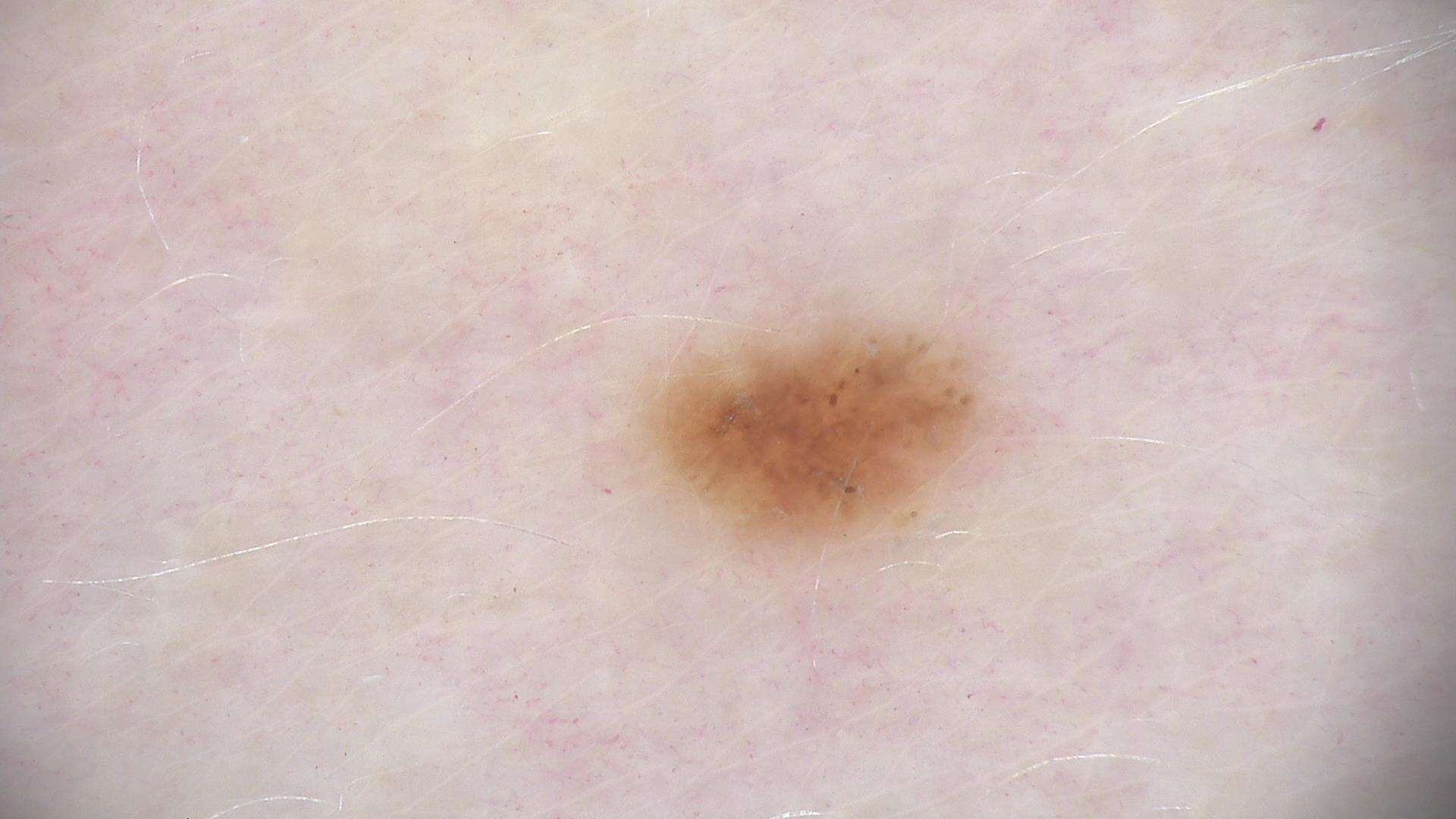A dermoscopic close-up of a skin lesion.
Labeled as a dysplastic junctional nevus.